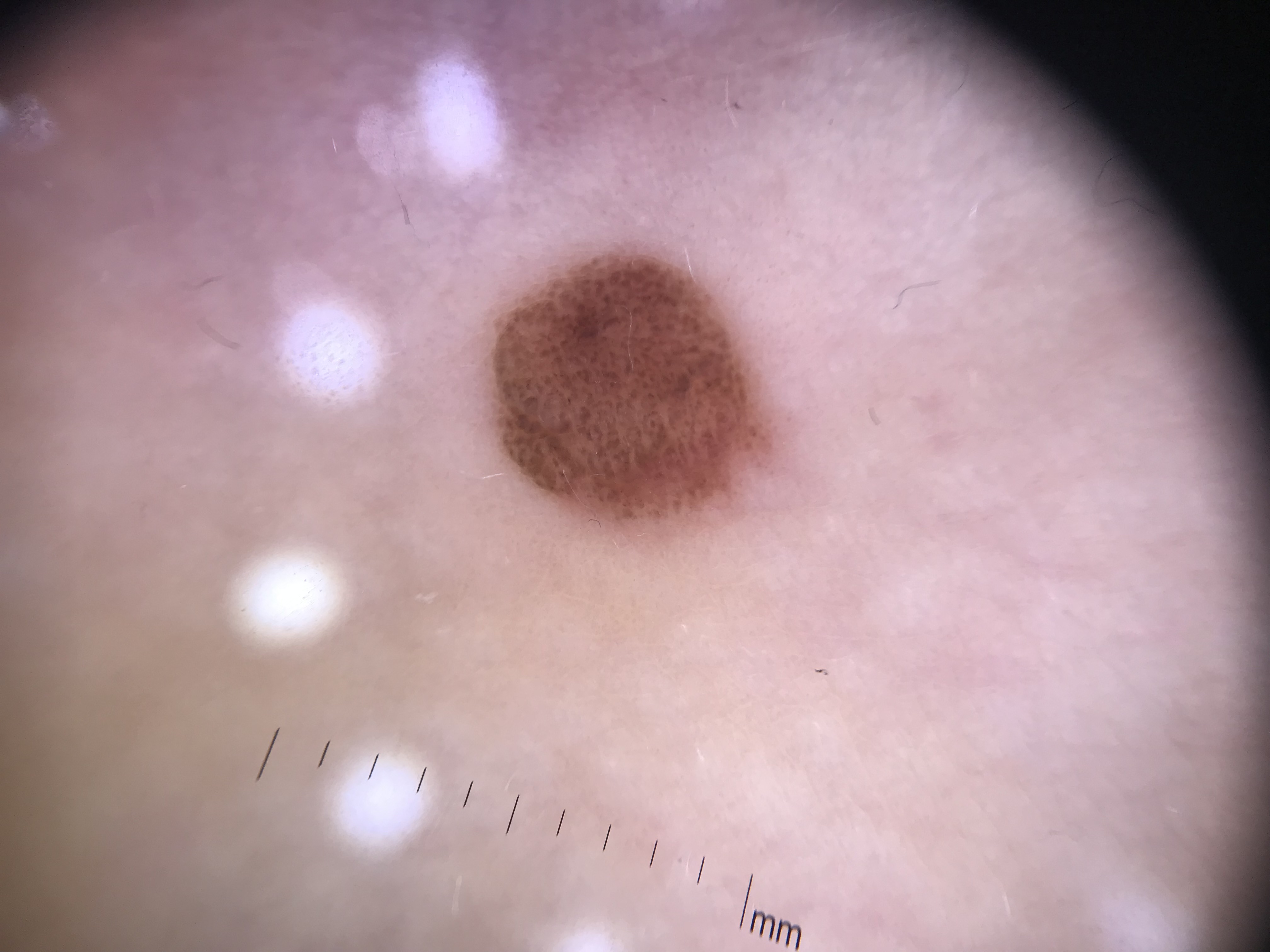{
  "diagnosis": {
    "name": "compound nevus",
    "code": "cb",
    "malignancy": "benign",
    "super_class": "melanocytic",
    "confirmation": "expert consensus"
  }
}